A dermoscopy image of a single skin lesion: 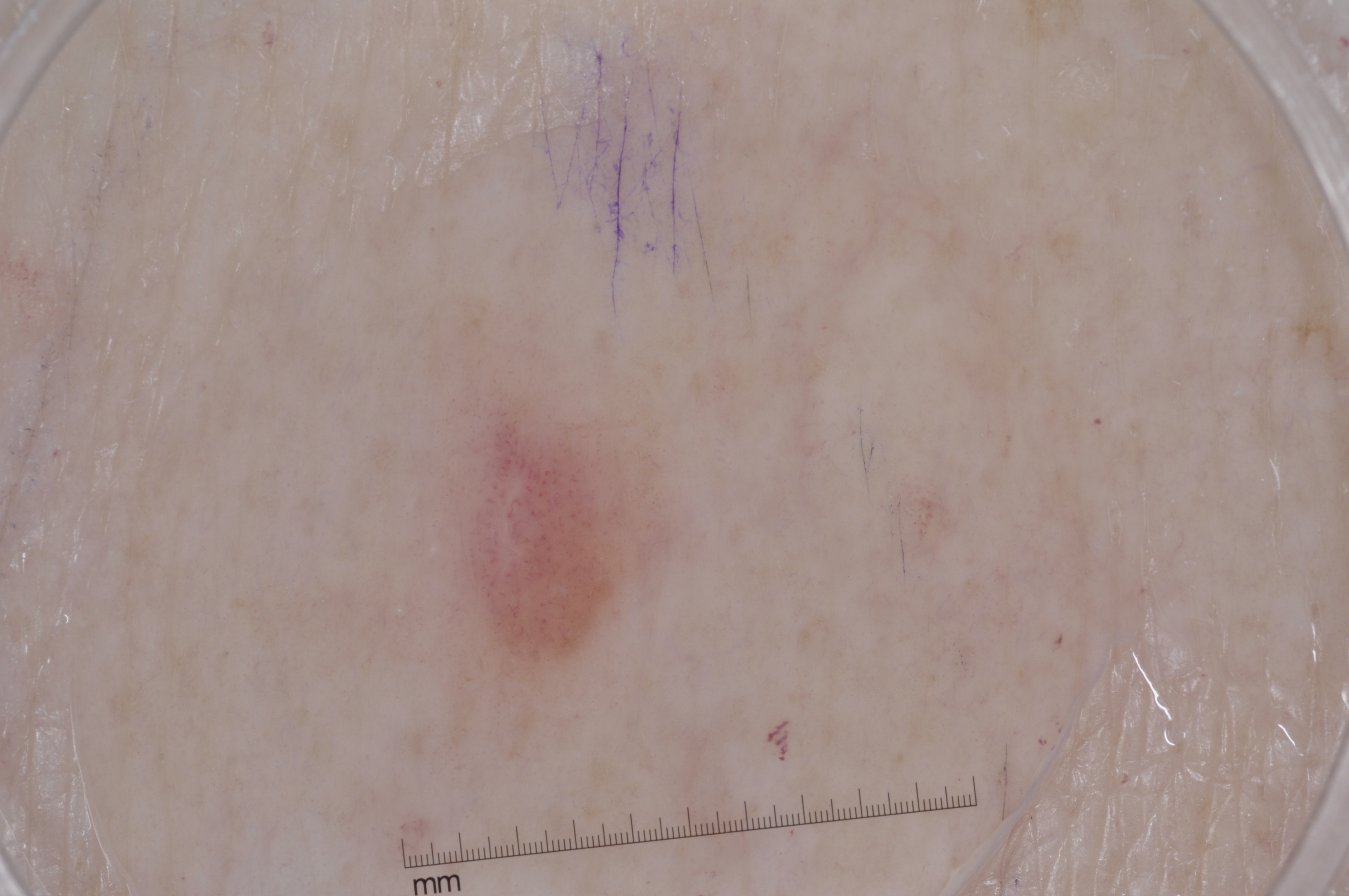lesion bbox = 433, 350, 674, 693 | dermoscopic pattern = milia-like cysts; absent: pigment network, streaks, and negative network | impression = a melanocytic nevus.